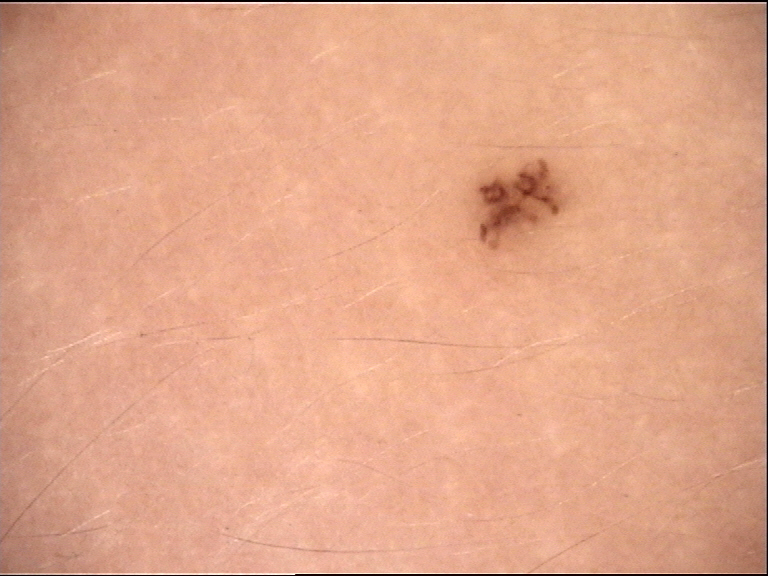assessment=junctional nevus (expert consensus).